This is a close-up image; the lesion involves the arm and leg:
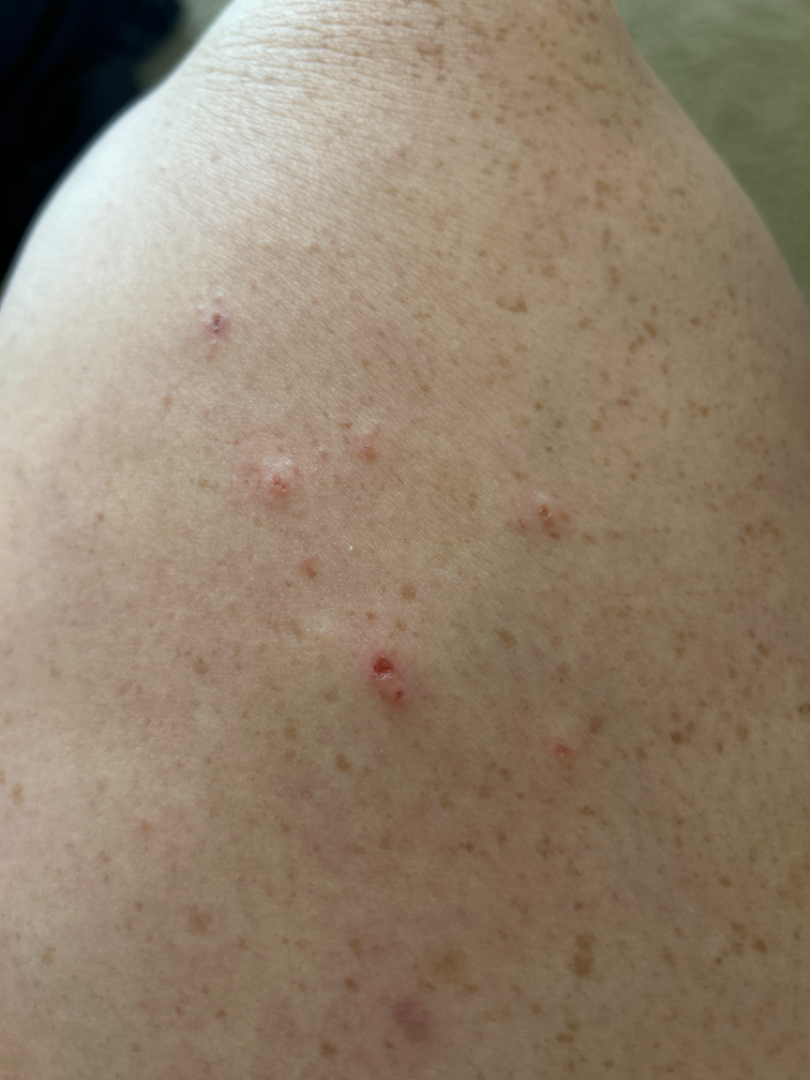Review:
On dermatologist assessment of the image: the primary impression is Prurigo nodularis; possibly Folliculitis.